Close-up view. Fitzpatrick phototype III.
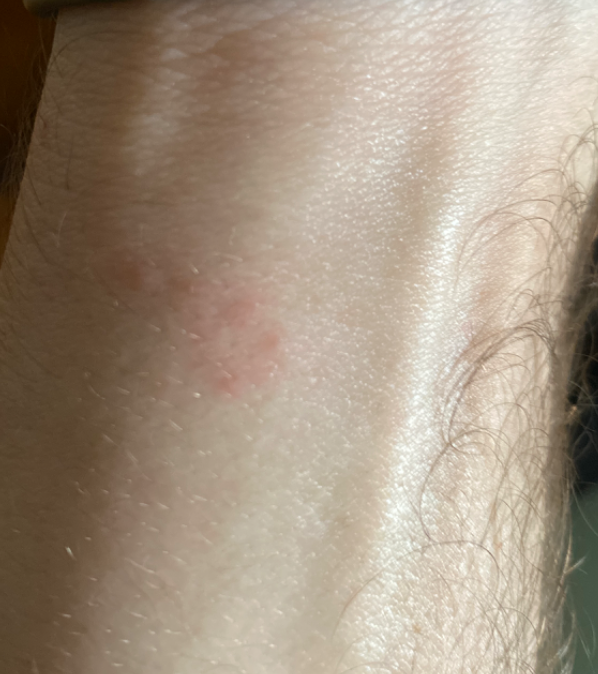assessment: the differential is split between Eczema, Allergic Contact Dermatitis and Irritant Contact Dermatitis